Self-categorized by the patient as a rash; the lesion is described as rough or flaky and flat; the affected area is the arm, leg, head or neck and palm; the contributor is a female aged 18–29; the patient reports associated joint pain and shortness of breath; this is a close-up image — 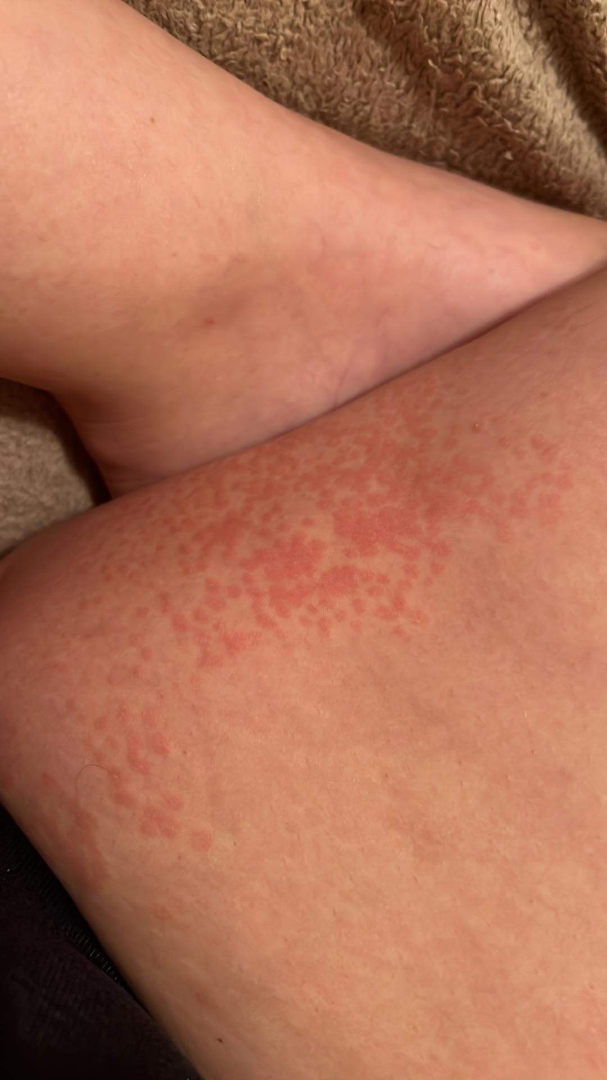diagnostic considerations — one reviewing dermatologist: favoring Eczema; also on the differential is Viral Exanthem; also consider Urticaria.